This image was taken at a distance.
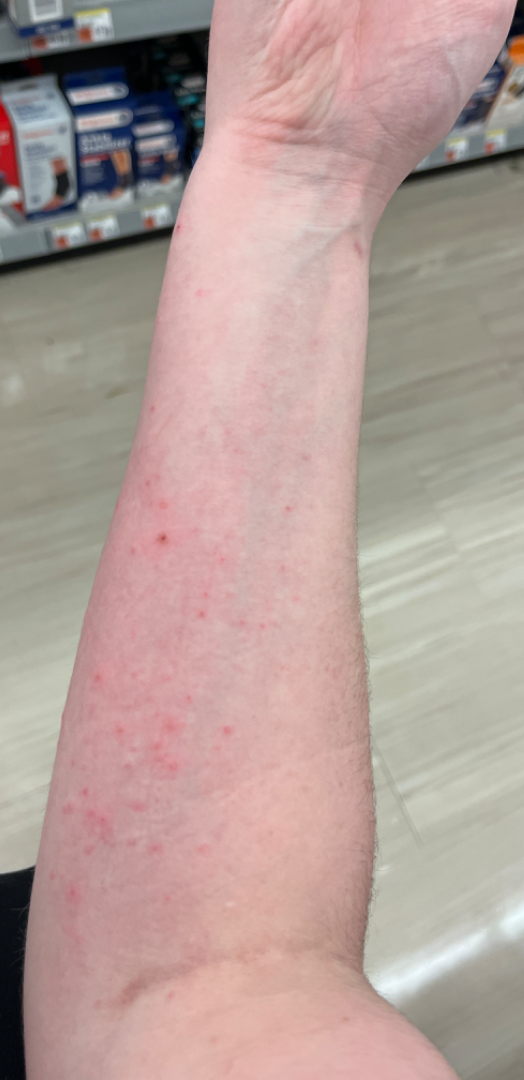impression=favoring Allergic Contact Dermatitis; also raised was Folliculitis; with consideration of Keratosis pilaris